This is a dermoscopic photograph of a skin lesion:
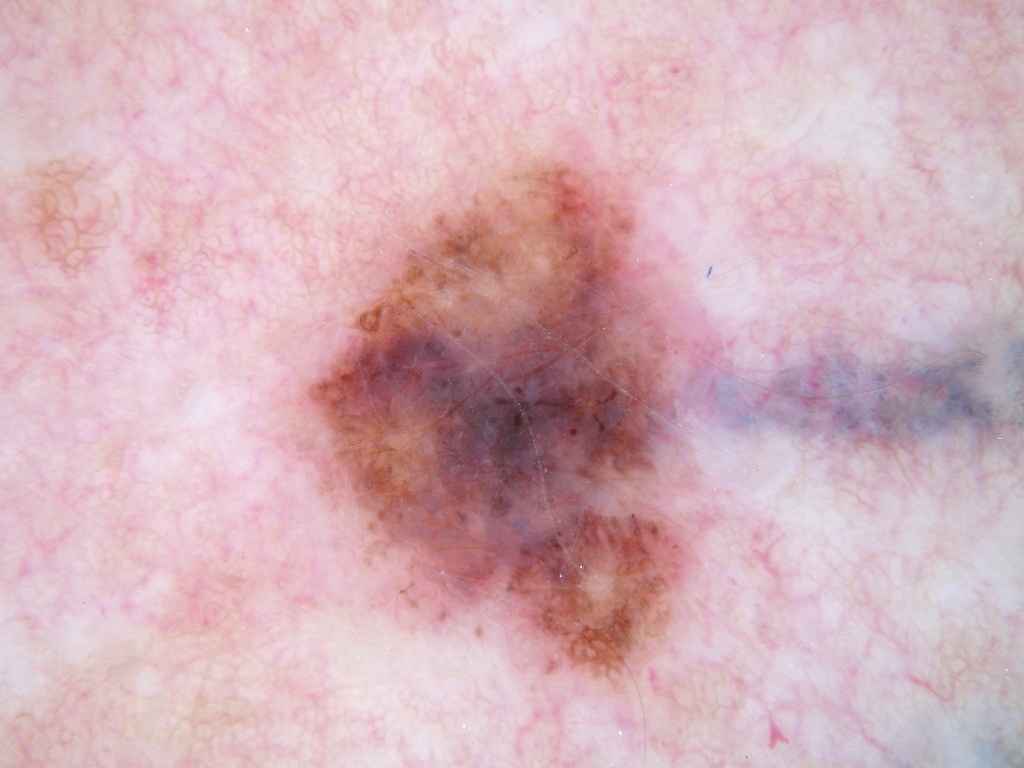On dermoscopy, the lesion shows globules and pigment network.
As (left, top, right, bottom), the lesion occupies the region 283/148/711/689.
The lesion takes up about 22% of the image.
Expert review diagnosed this as a melanocytic nevus.